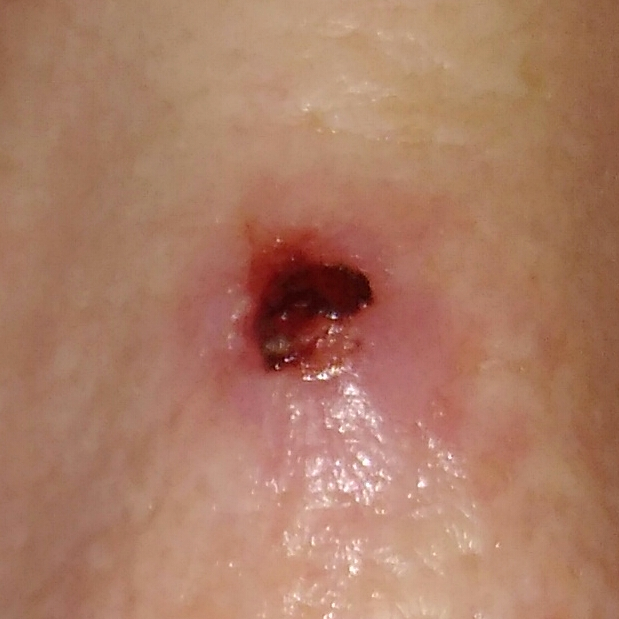Histopathological examination showed a basal cell carcinoma.